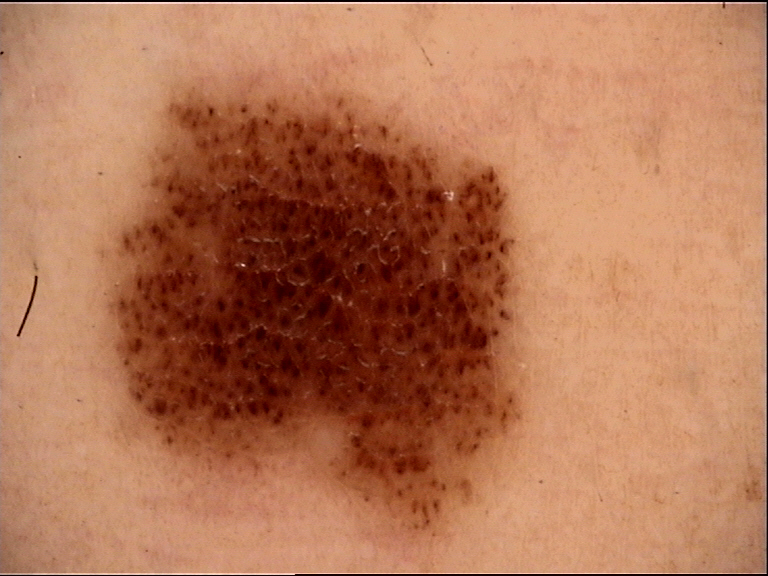Q: What is this lesion?
A: compound nevus (expert consensus)